A close-up photograph; the lesion involves the top or side of the foot; male contributor, age 40–49:
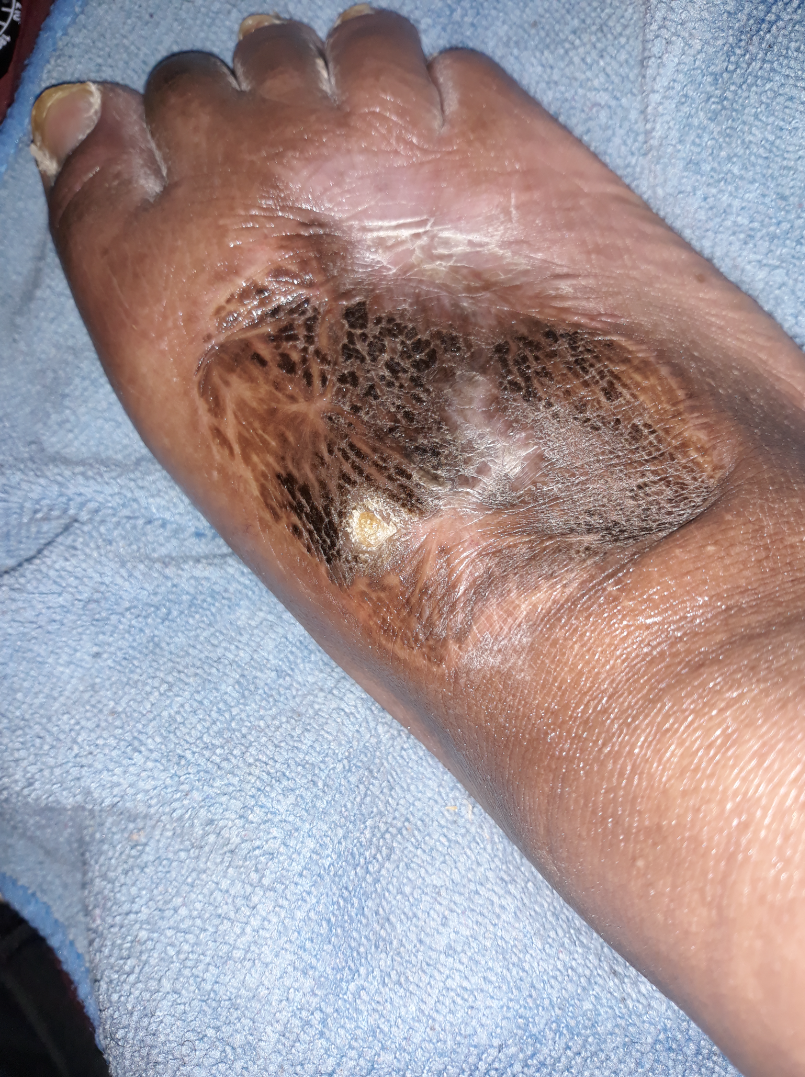duration: more than one year
differential:
  leading:
    - Foot ulcer
  considered:
    - Mixed diabetic ulcer - foot
    - Deep fungal infection